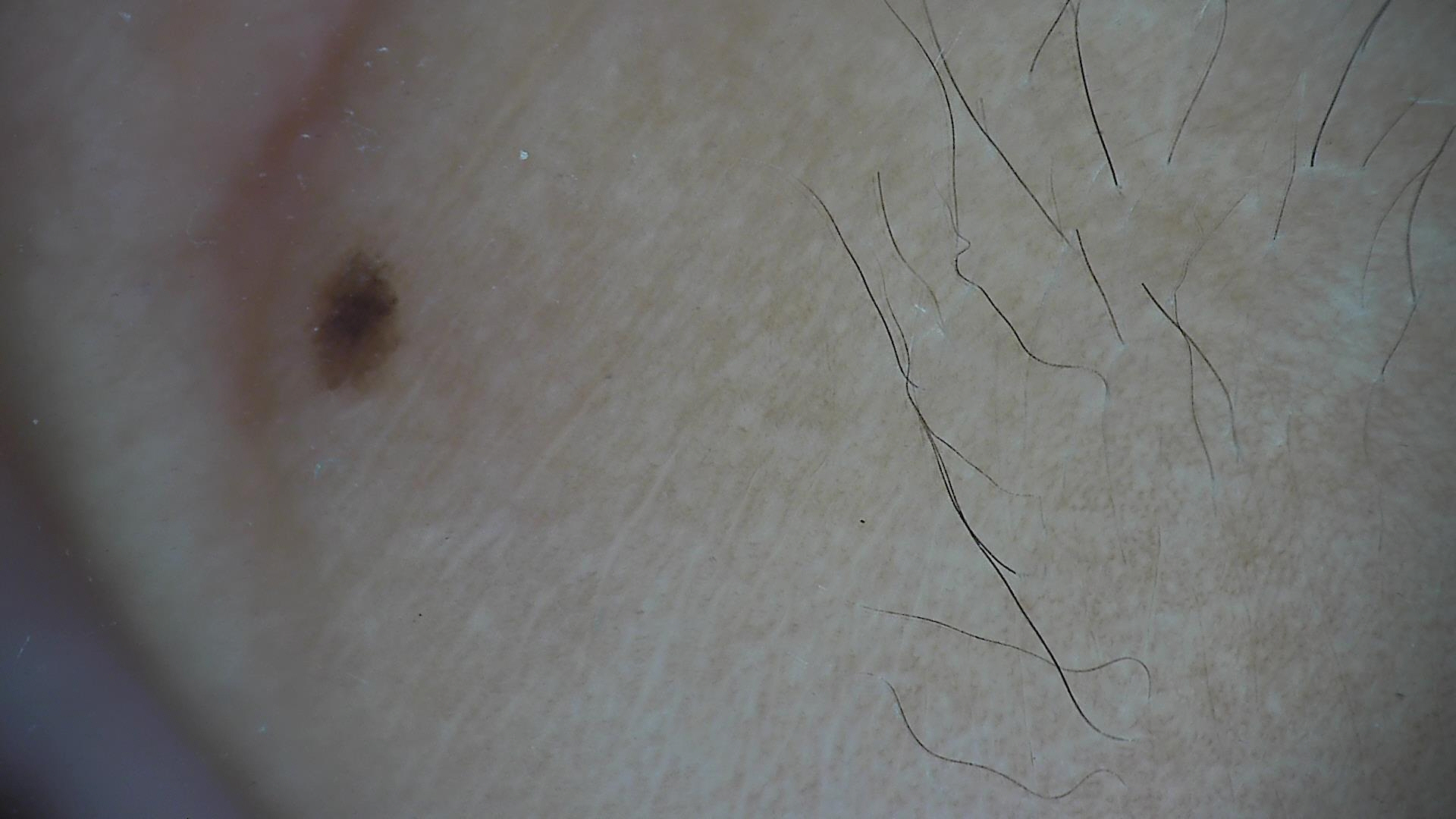Q: What is the imaging modality?
A: dermatoscopy
Q: What was the diagnostic impression?
A: dysplastic junctional nevus (expert consensus)